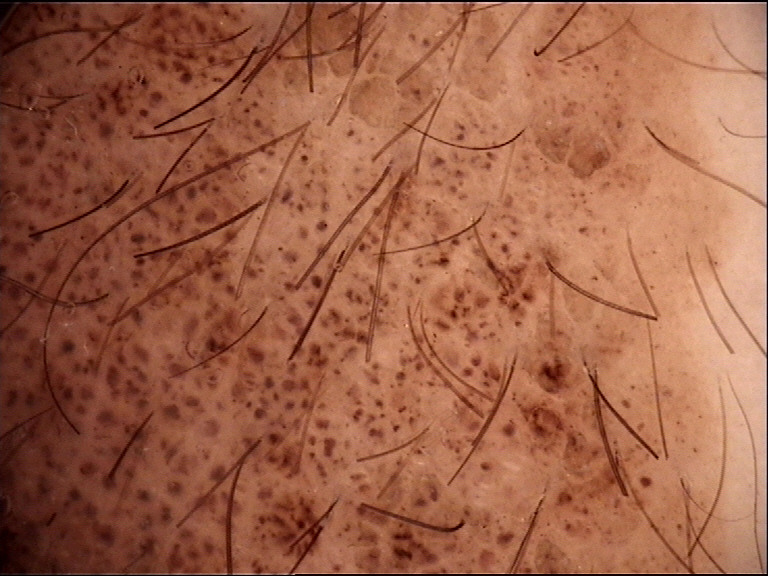Findings:
A dermoscopy image of a single skin lesion.
Impression:
The diagnosis was a banal lesion — a congenital compound nevus.